A female subject age 73:
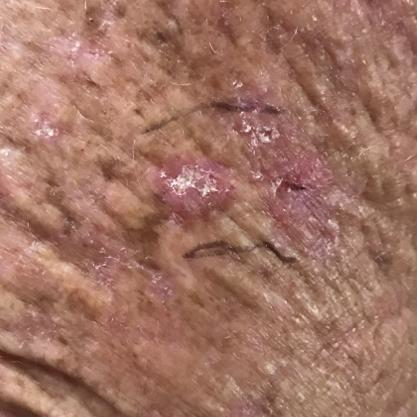region=a forearm
patient-reported symptoms=pain, itching
impression=actinic keratosis (clinical consensus)